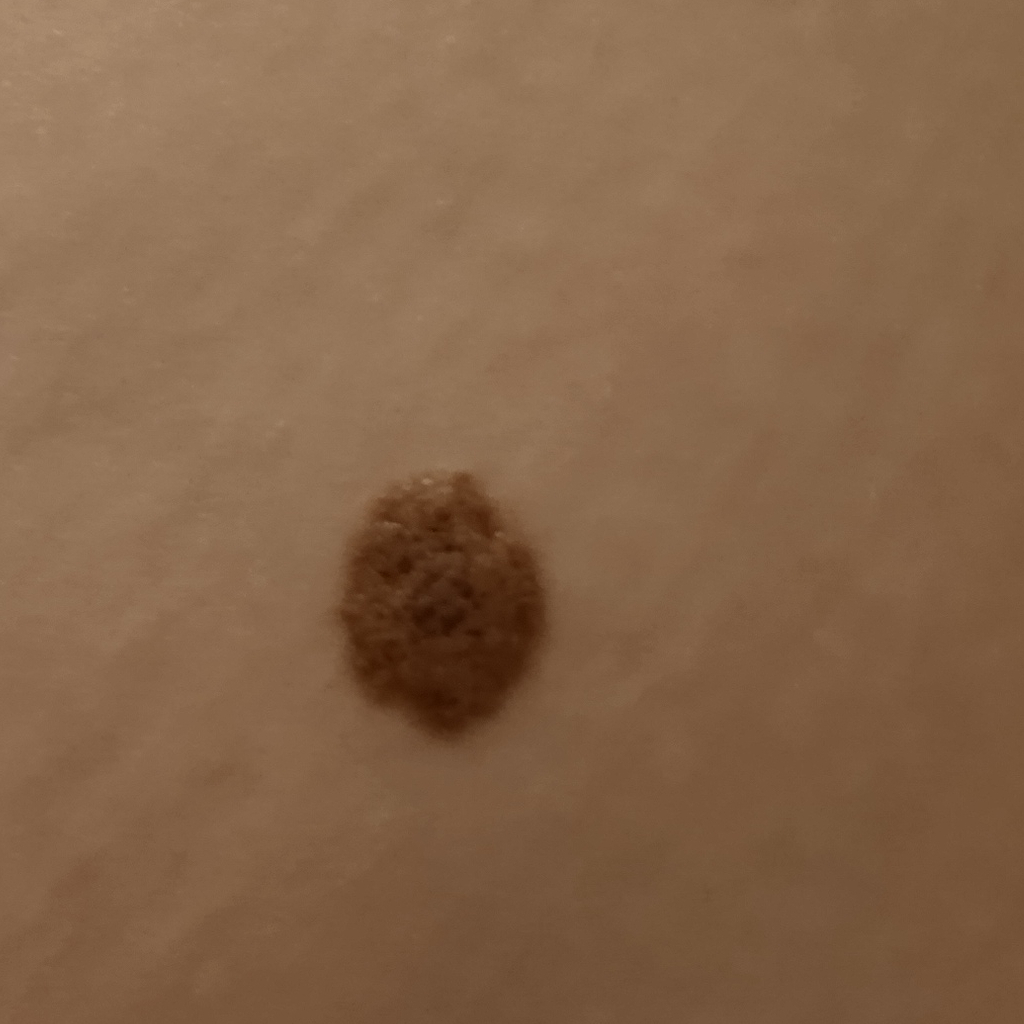Collected as part of a research study, without a referral diagnosis.
The patient says their skin reddens with sun exposure.
By self-report, a history of sunbed use.
A macroscopic clinical photograph of a skin lesion.
A female subject 26 years old.
The patient describes having numerous moles.
The lesion is on the torso.
The lesion measures approximately 12.1 mm.
The dermatologists' assessment was a melanocytic nevus.